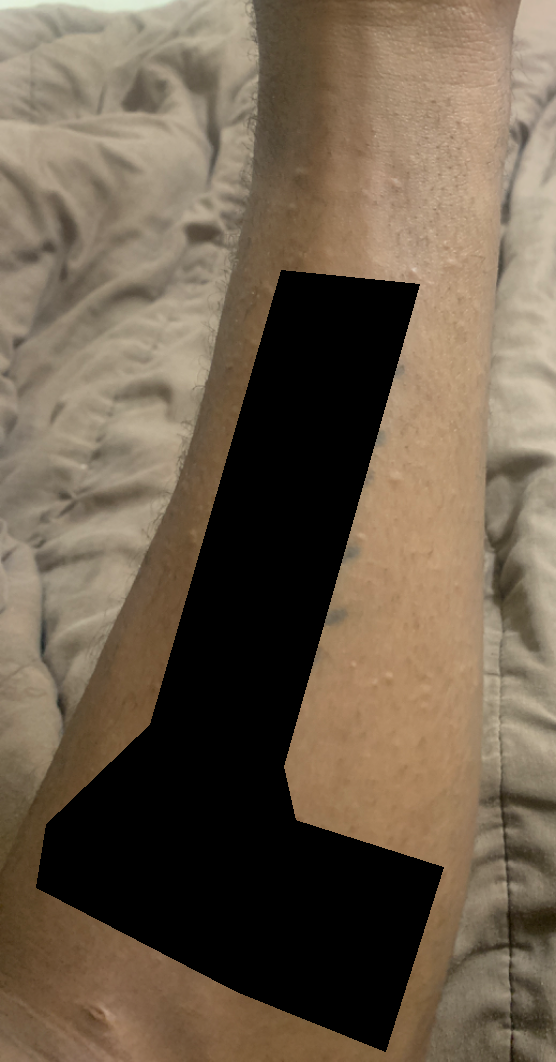History: FST IV. The photograph was taken at a distance. The arm is involved. The patient considered this a rash. No associated systemic symptoms reported. Reported lesion symptoms include itching. Present for about one day. The subject is a male aged 30–39. The patient indicates the lesion is raised or bumpy. Impression: Reviewed remotely by three dermatologists: most consistent with Lichenoid myxedema; possibly Clinical neurofibromatosis.